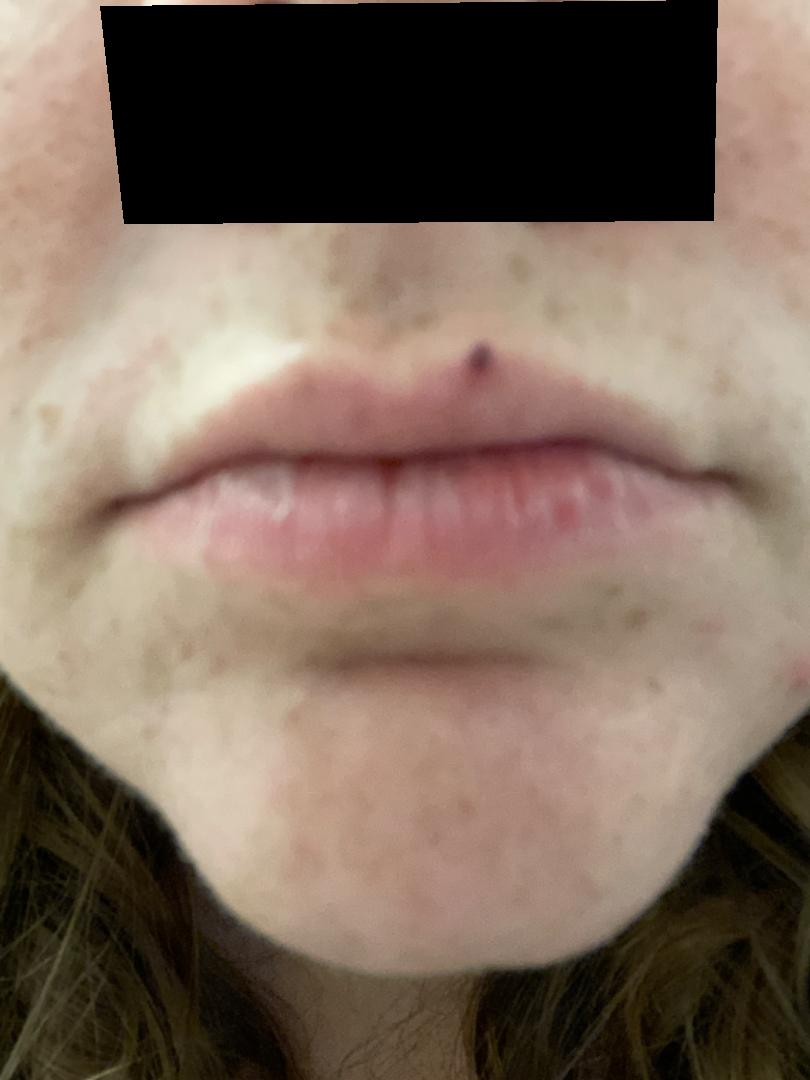| field | value |
|---|---|
| assessment | not assessable |
| view | close-up |